An image taken at a distance; the patient also reports fatigue and joint pain; the patient considered this skin that appeared healthy to them; the leg is involved; the contributor is 60–69, female; the patient reports enlargement and bothersome appearance:
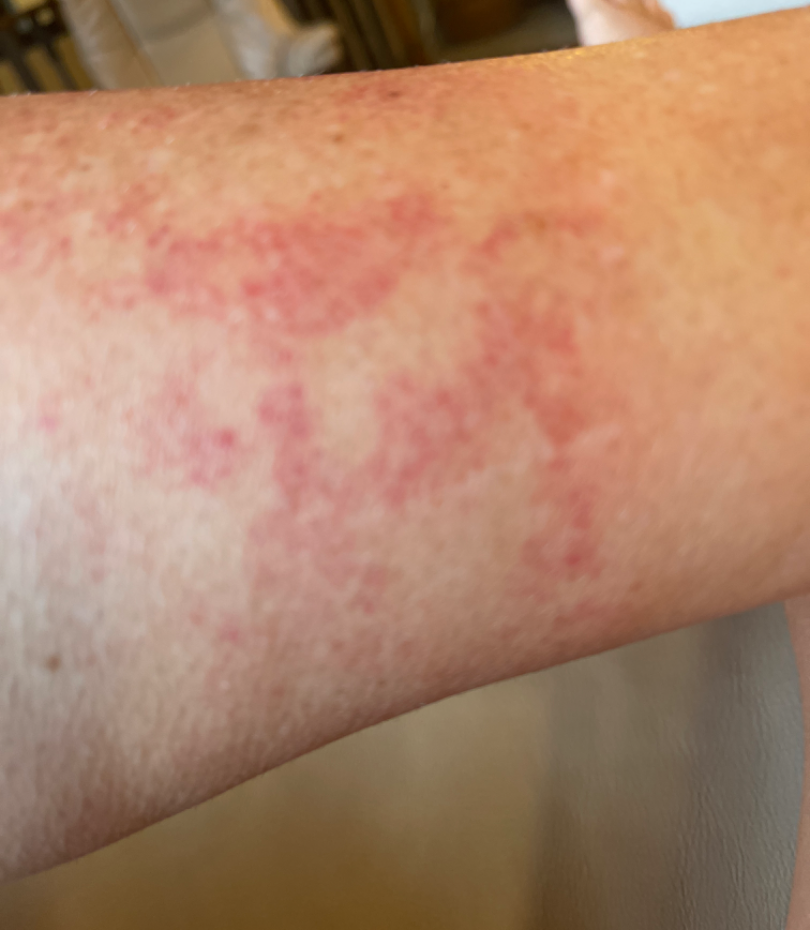{"differential": {"leading": ["Pigmented purpuric eruption"]}}